A dermoscopy image of a single skin lesion.
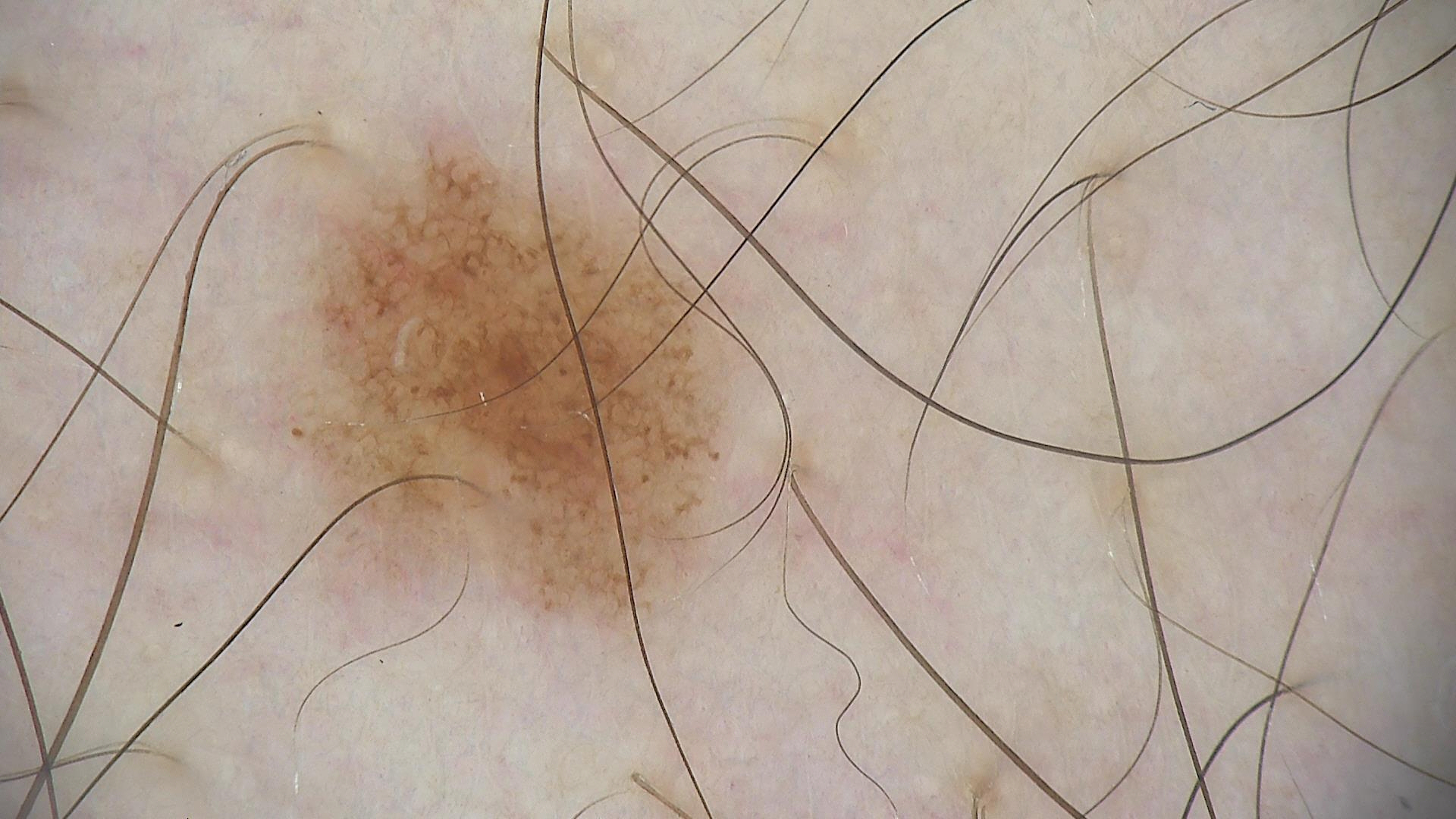Case:
• label · dysplastic junctional nevus (expert consensus)